Contact-polarized dermoscopy of a skin lesion; a female subject aged 33-37; Fitzpatrick II.
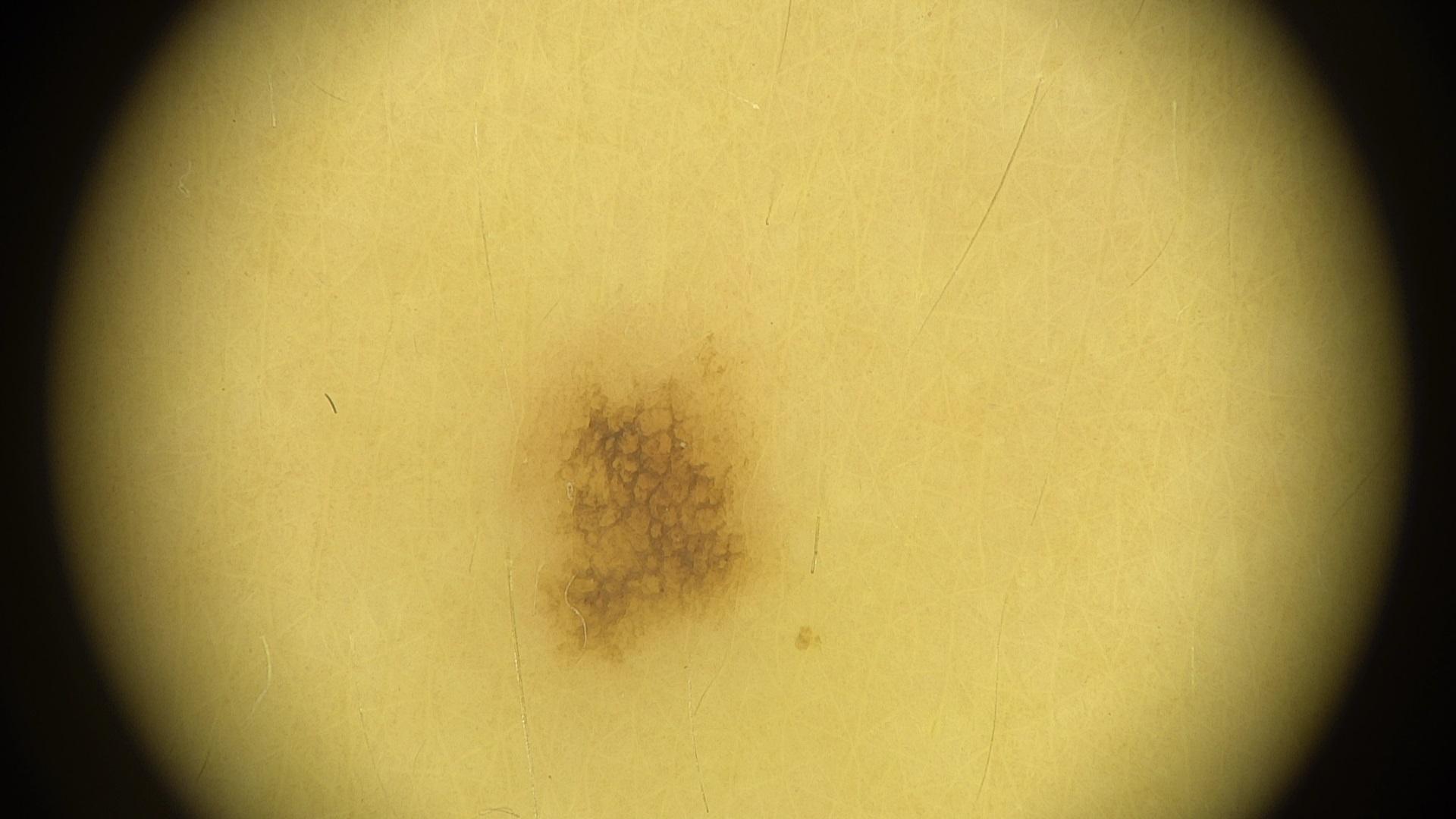{
  "lesion_location": {
    "region": "the trunk",
    "detail": "the posterior trunk"
  },
  "diagnosis": {
    "name": "Nevus",
    "malignancy": "benign",
    "confirmation": "expert clinical impression",
    "lineage": "melanocytic"
  }
}